The contributor is a male aged 70–79, the photograph is a close-up of the affected area, the lesion involves the leg — 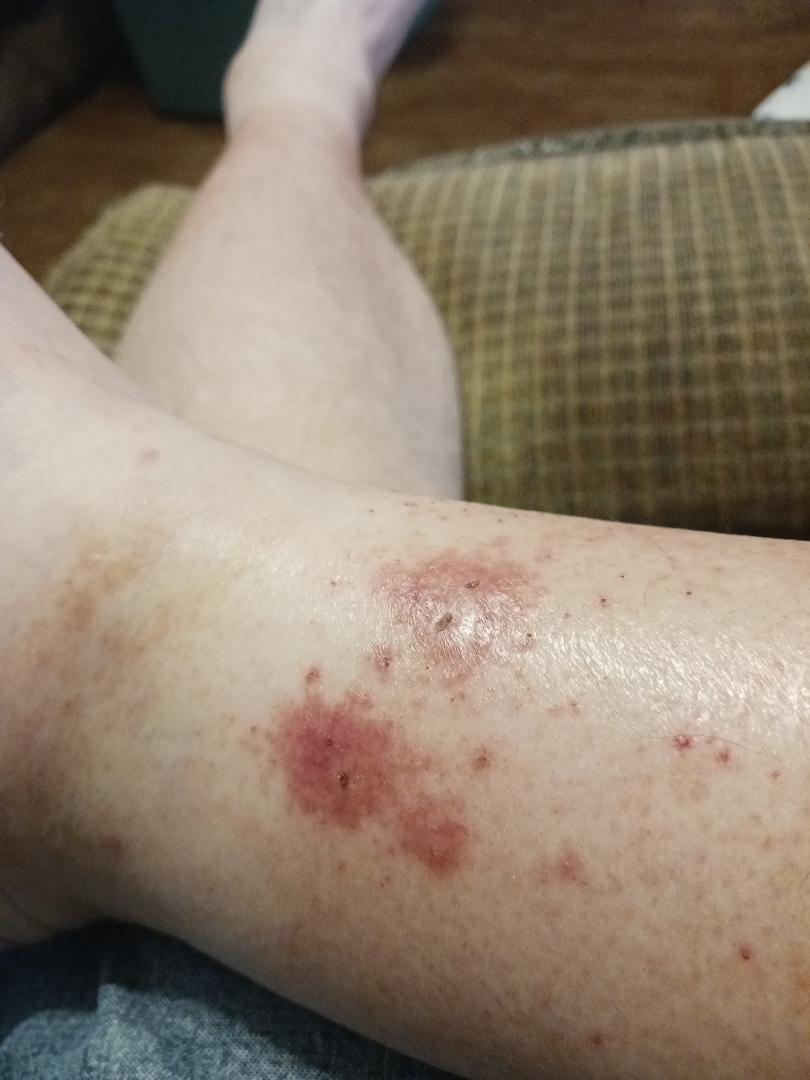* other reported symptoms — none reported
* lesion texture — rough or flaky
* skin tone — Fitzpatrick III; lay reviewers estimated Monk Skin Tone 2 or 3
* onset — one to four weeks
* differential diagnosis — in keeping with Pigmented purpuric eruption